A contact-polarized dermoscopy image of a skin lesion. A female subject aged approximately 80. Recorded as skin type II — 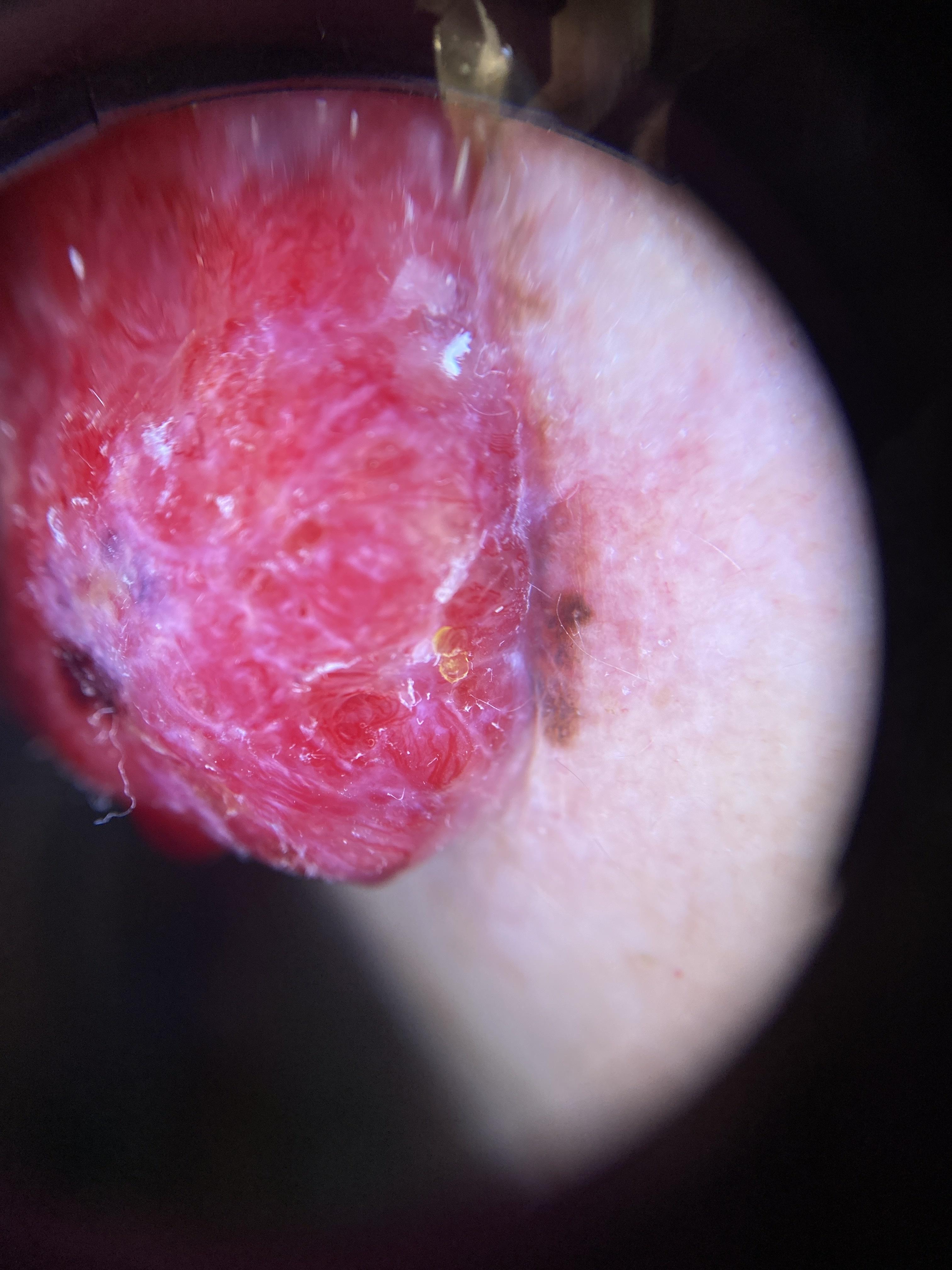The lesion is on an upper extremity.
Biopsy-confirmed as a melanoma.